The condition has been present for one to four weeks. Close-up view. The patient reported no systemic symptoms. The patient considered this a rash. The lesion involves the palm. The lesion is associated with itching.
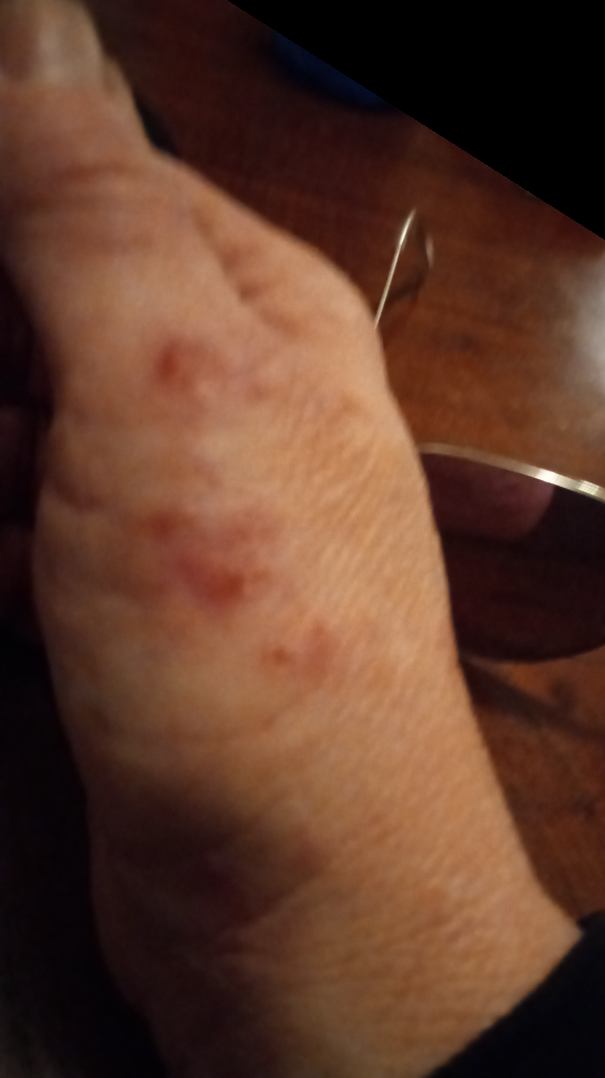The reviewing dermatologist was unable to assign a differential diagnosis from the image.